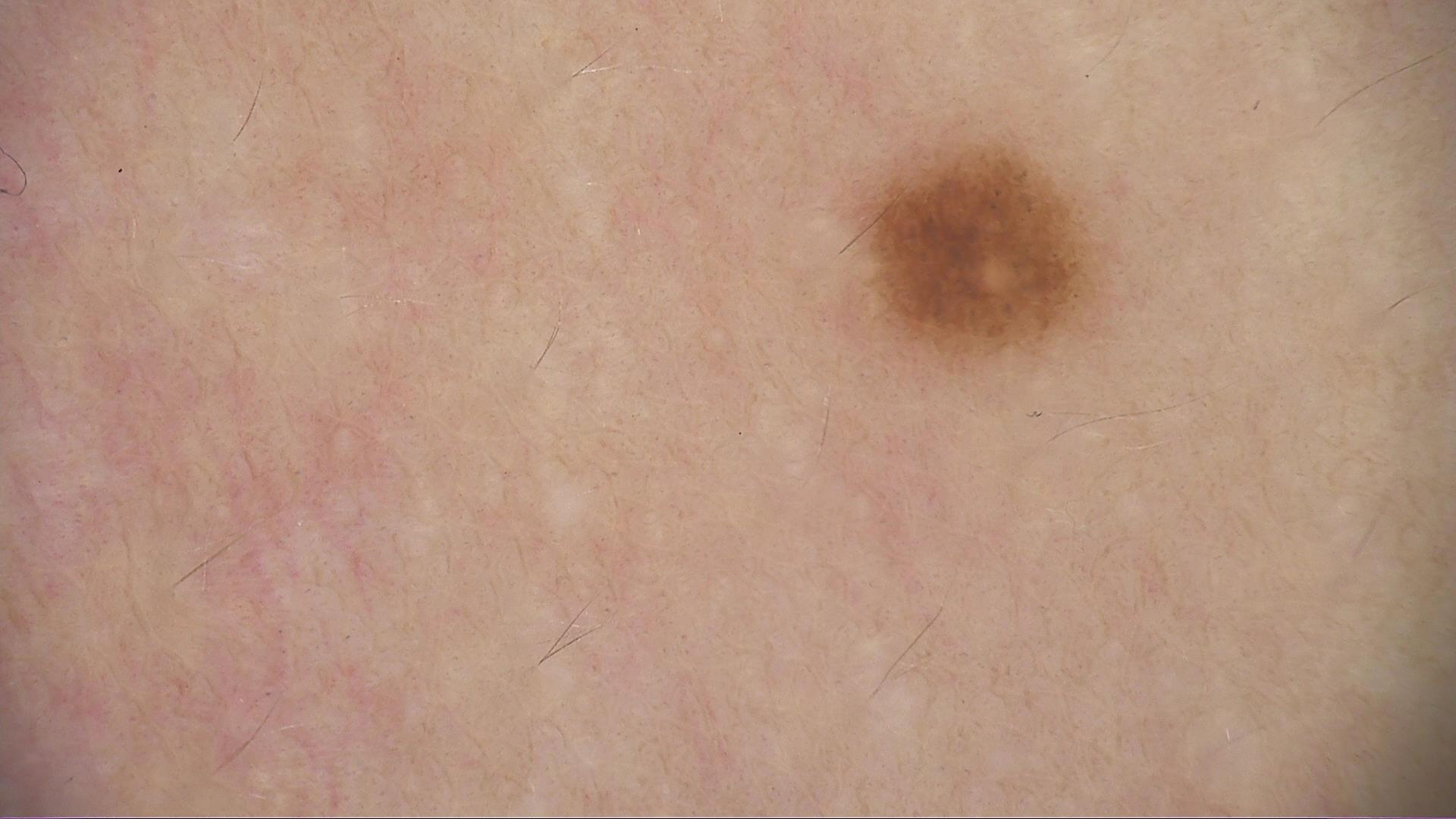{"image": "dermoscopy", "lesion_type": {"main_class": "banal", "pattern": "junctional"}, "diagnosis": {"name": "junctional nevus", "code": "jb", "malignancy": "benign", "super_class": "melanocytic", "confirmation": "expert consensus"}}